A dermatoscopic image of a skin lesion.
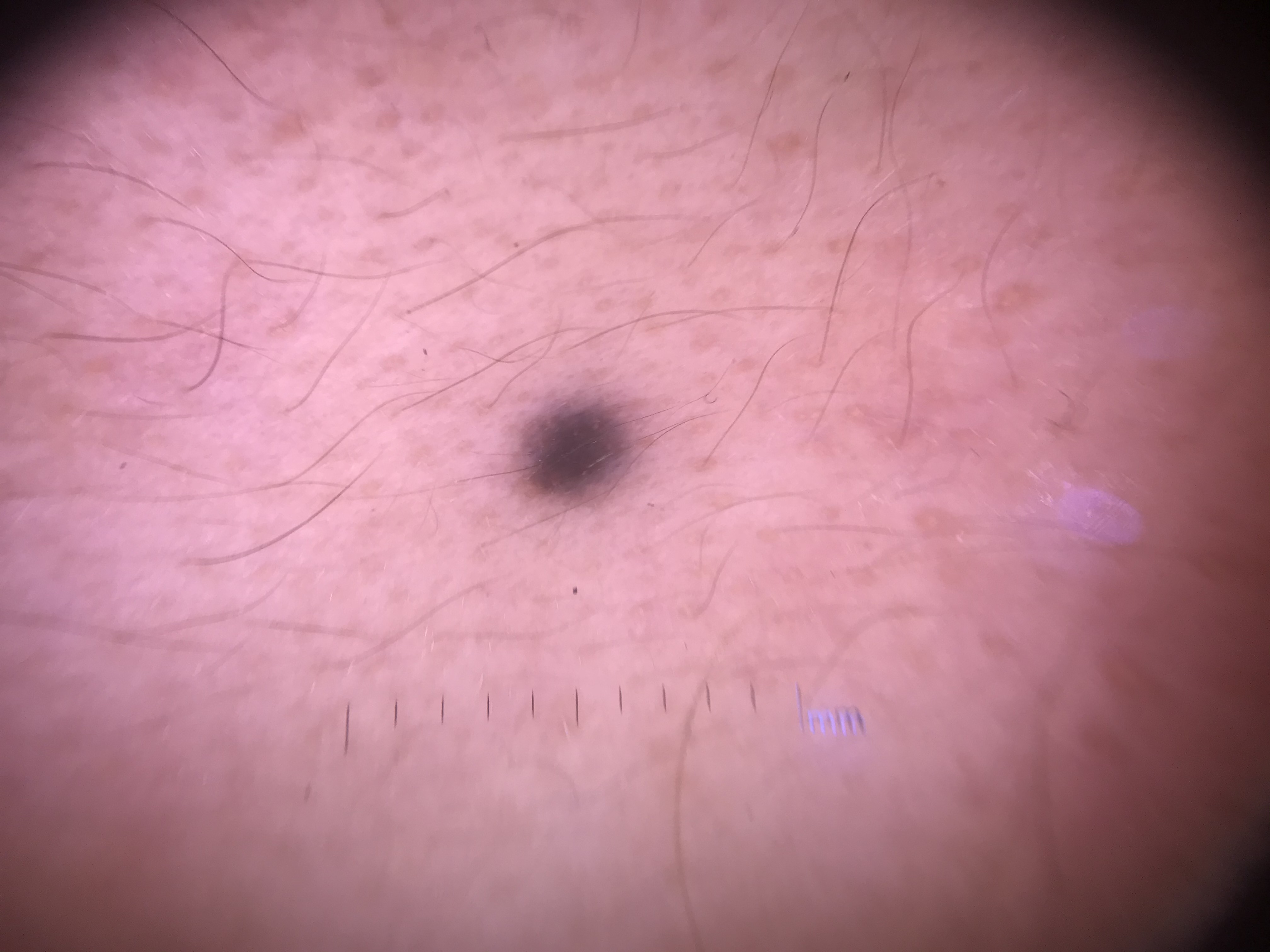Q: What is the lesion category?
A: banal, dermal
Q: What was the diagnostic impression?
A: blue nevus (expert consensus)